A dermoscopic close-up of a skin lesion.
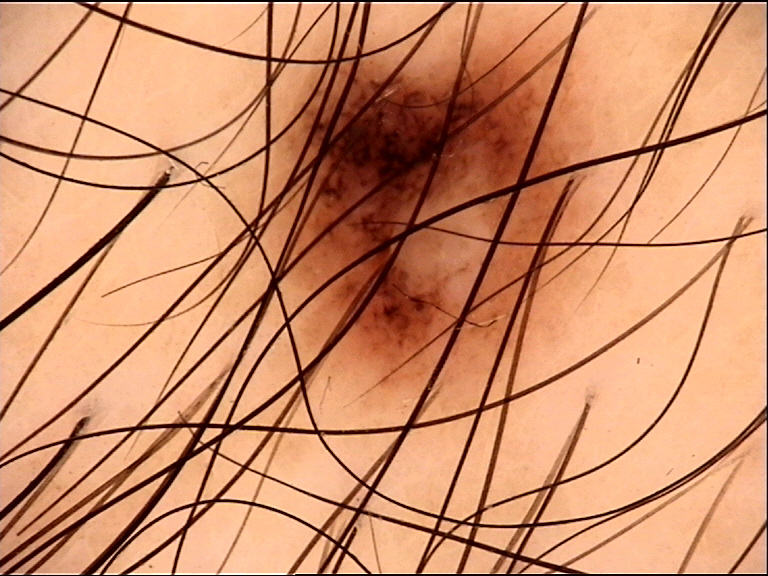| feature | finding |
|---|---|
| assessment | junctional nevus (expert consensus) |